The affected area is the sole of the foot · the photograph is a close-up of the affected area — 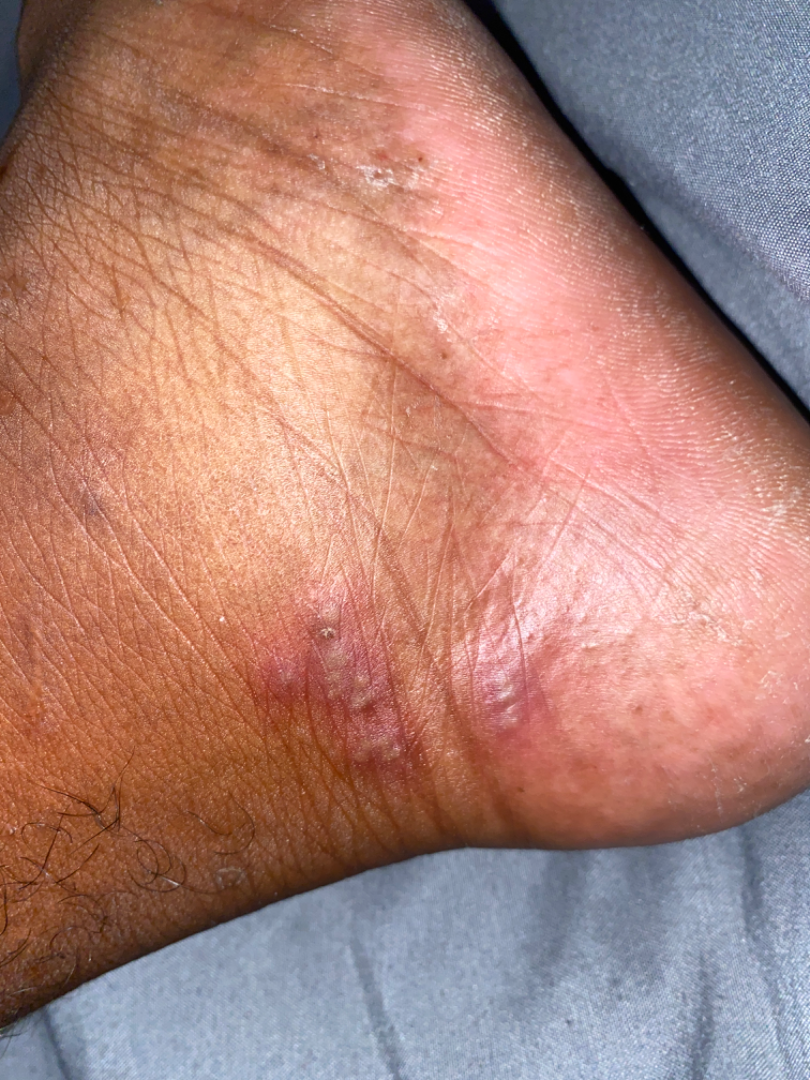The case was difficult to assess from the available photograph.